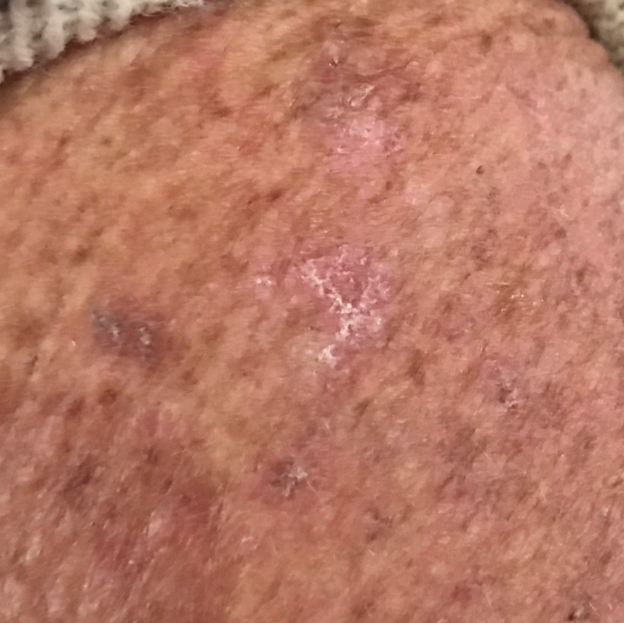A subject 50 years old. The clinical impression was an actinic keratosis.